Close-up view · texture is reported as rough or flaky · the patient reports the condition has been present for three to twelve months · symptoms reported: bothersome appearance and itching · the subject is a female aged 18–29 · the patient described the issue as a nail problem — 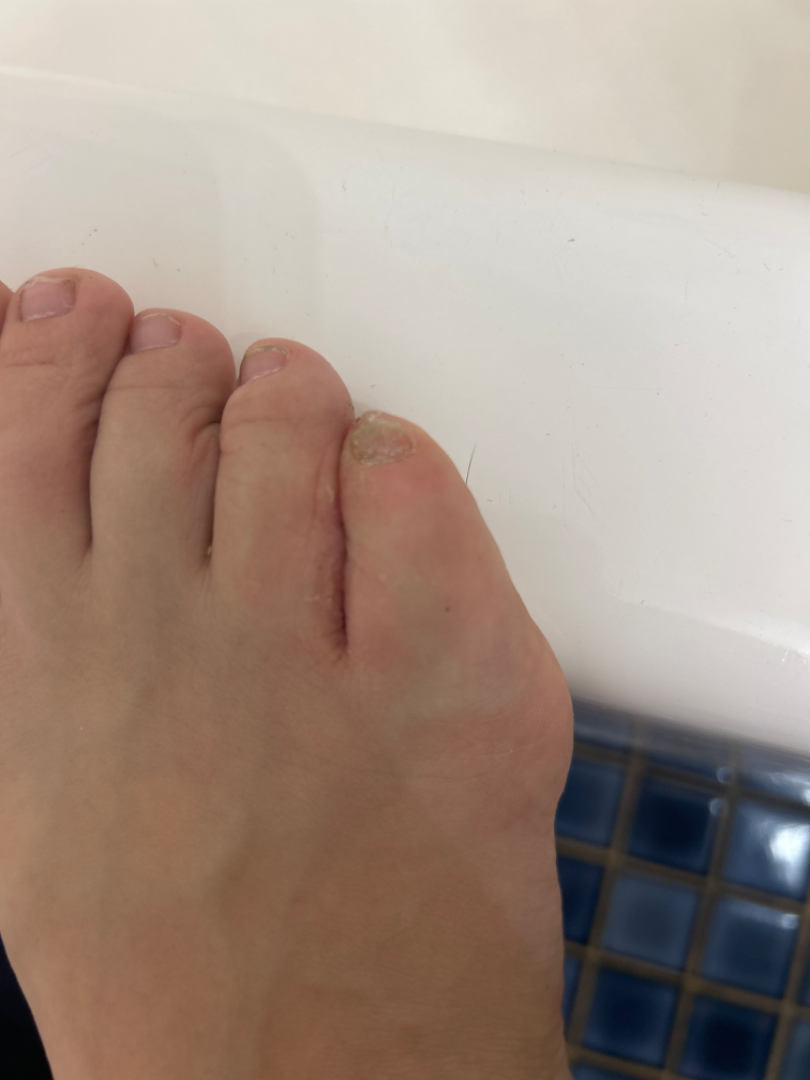Q: Could the case be diagnosed?
A: unable to determine